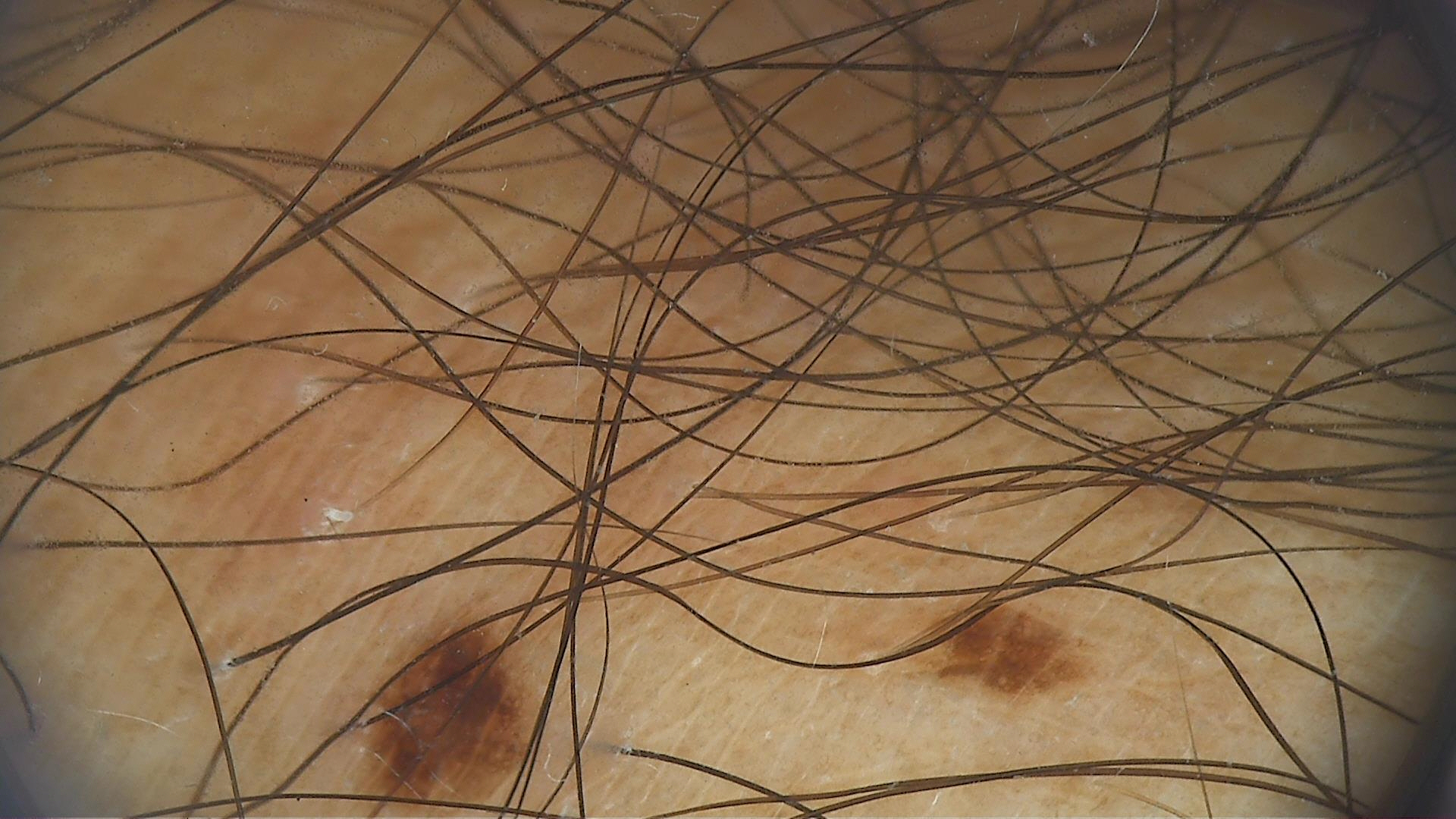Diagnosed as a benign lesion — a dysplastic junctional nevus.